A dermoscopic image of a skin lesion.
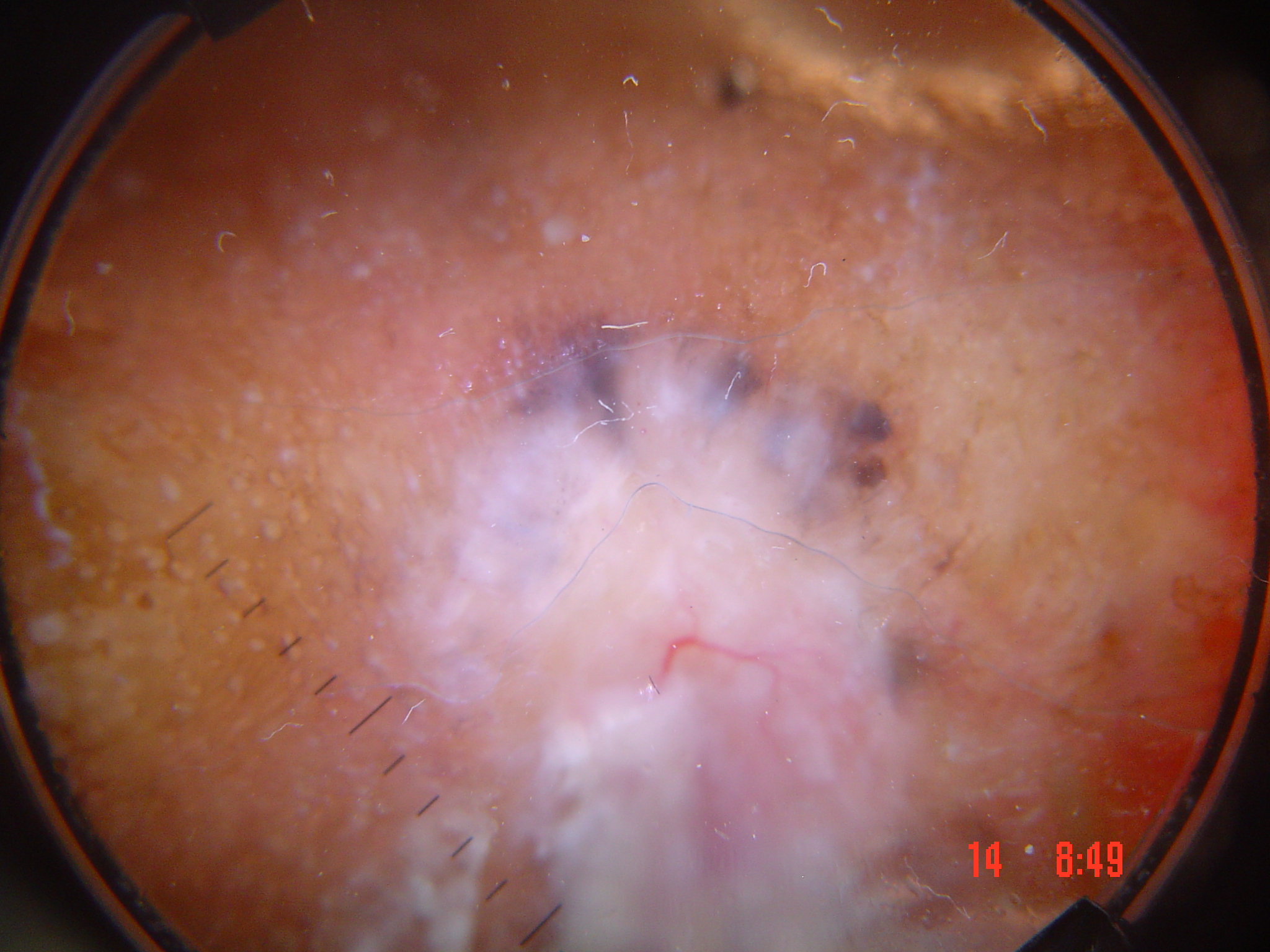category = keratinocytic, diagnostic label = basal cell carcinoma (biopsy-proven).